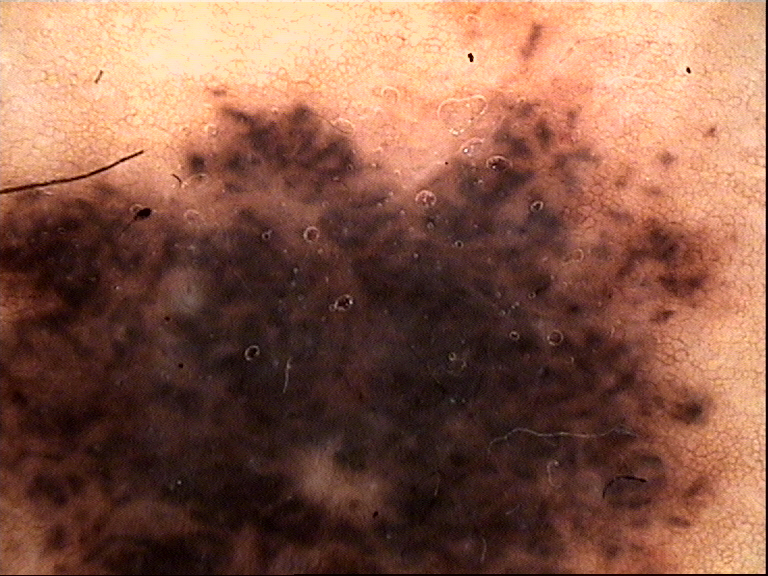Conclusion: Consistent with a banal lesion — a congenital compound nevus.